A male subject age 66 · acquired for a research image collection, with no referral diagnosis · the patient describes having few moles overall · by self-report, a prior organ transplant, no immunosuppression, and no personal history of skin cancer:
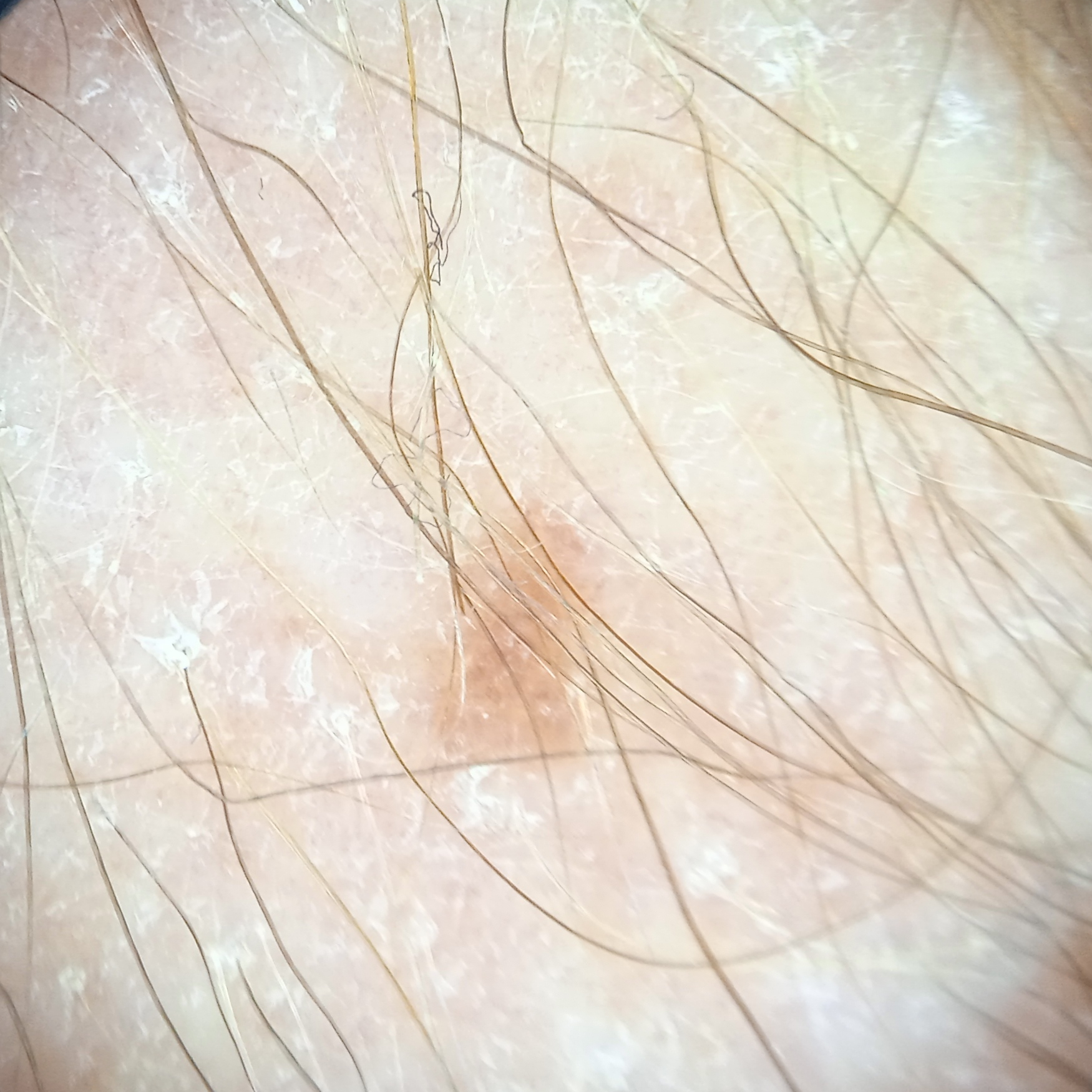Clinical context: The lesion involves an arm. Measuring roughly 3.4 mm. Conclusion: The dermatologists' assessment was a melanocytic nevus.